The lesion involves the arm, an image taken at a distance: 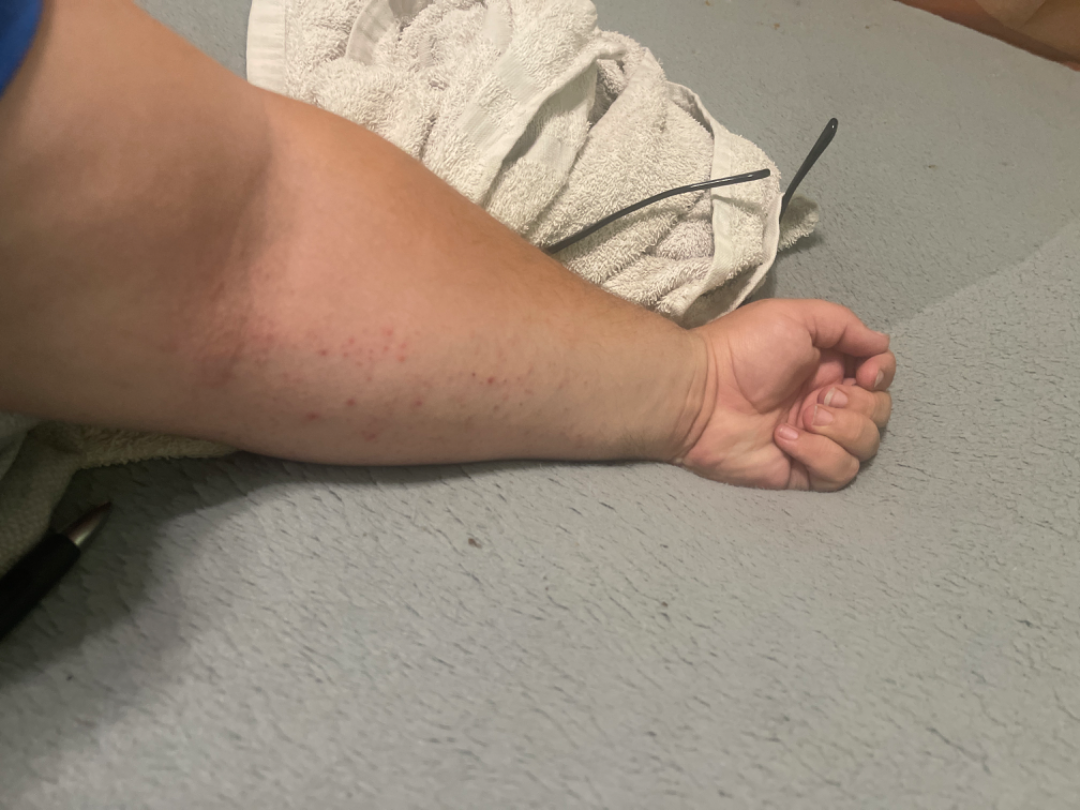clinical impression = Eczema (most likely).